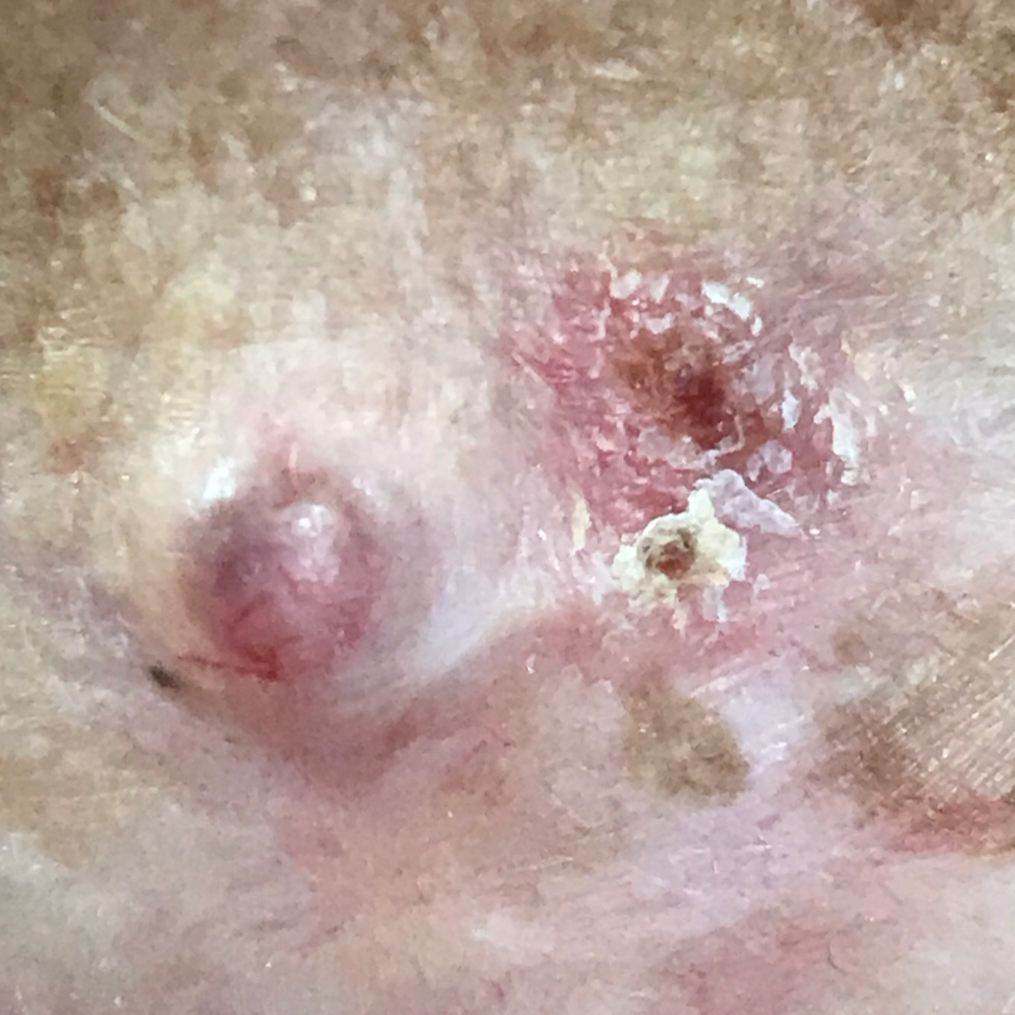Confirmed on histopathology as a basal cell carcinoma.